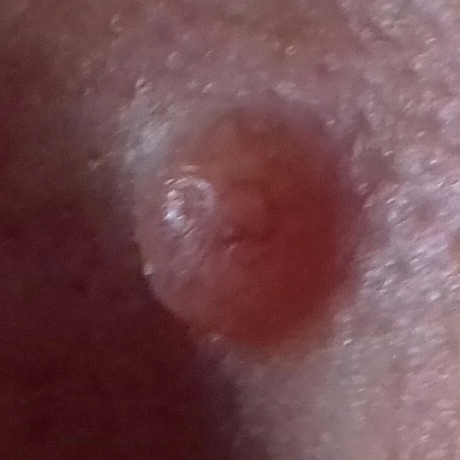Findings:
A clinical close-up photograph of a skin lesion. History notes alcohol use, pesticide exposure, and no prior skin cancer (patient or family). Located on the face. Measuring about 60 × 40 mm. Per patient report, the lesion is elevated.
Diagnosis:
Histopathology confirmed a nevus.